The affected area is the head or neck; reported duration is less than one week; the patient is a male aged 18–29; this is a close-up image; the lesion is described as raised or bumpy:
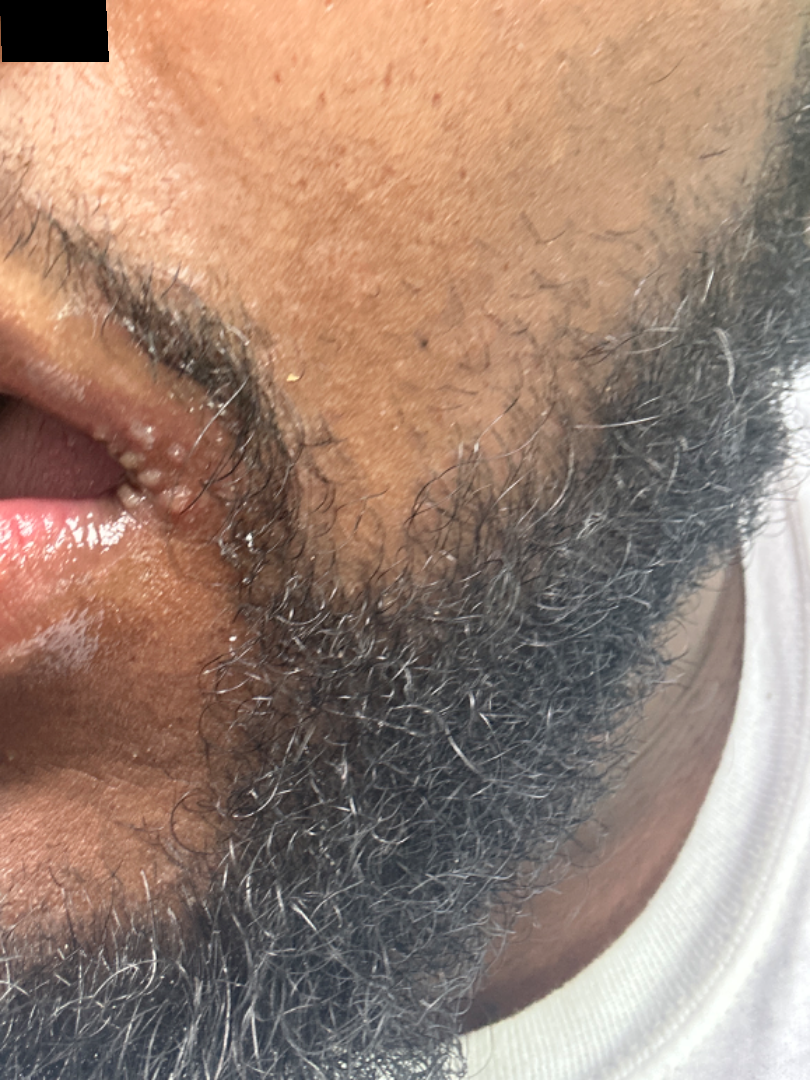Reviewed remotely by one dermatologist: in keeping with Herpes Simplex.